The lesion involves the arm · this is a close-up image · the patient is 18–29, female: 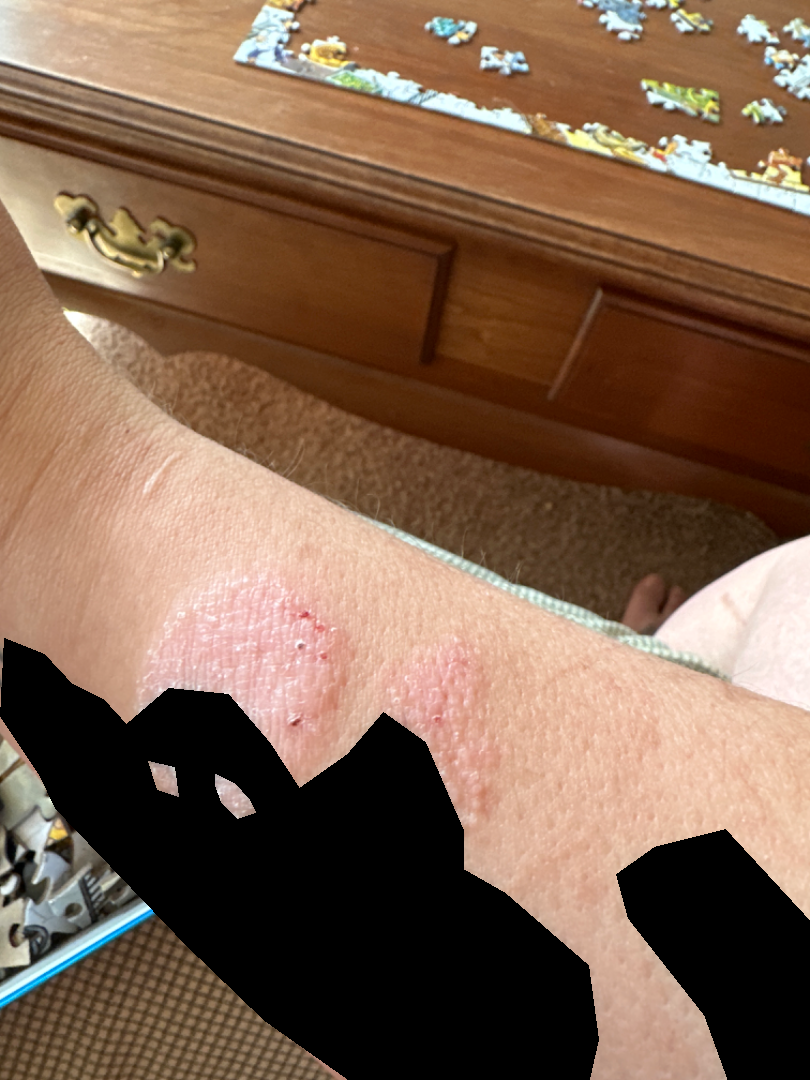Review:
On teledermatology review, favoring Psoriasis; possibly Eczema; less likely is Tinea.